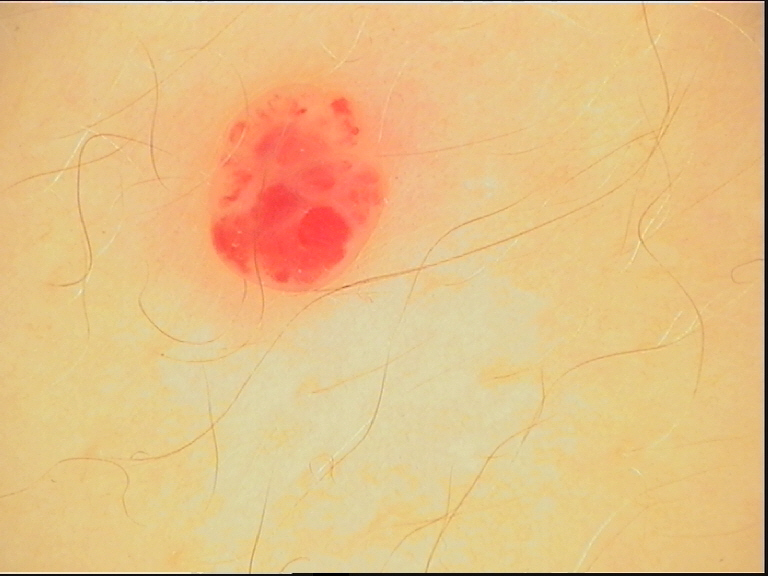<lesion>
  <image>dermoscopy</image>
  <lesion_type>
    <main_class>vascular</main_class>
  </lesion_type>
  <diagnosis>
    <name>hemangioma</name>
    <code>ha</code>
    <malignancy>benign</malignancy>
    <super_class>non-melanocytic</super_class>
    <confirmation>expert consensus</confirmation>
  </diagnosis>
</lesion>